A female patient in their mid-50s · history notes alcohol use and prior malignancy (patient or family) · the patient was assessed as Fitzpatrick phototype IV · a clinical photo of a skin lesion taken with a smartphone: 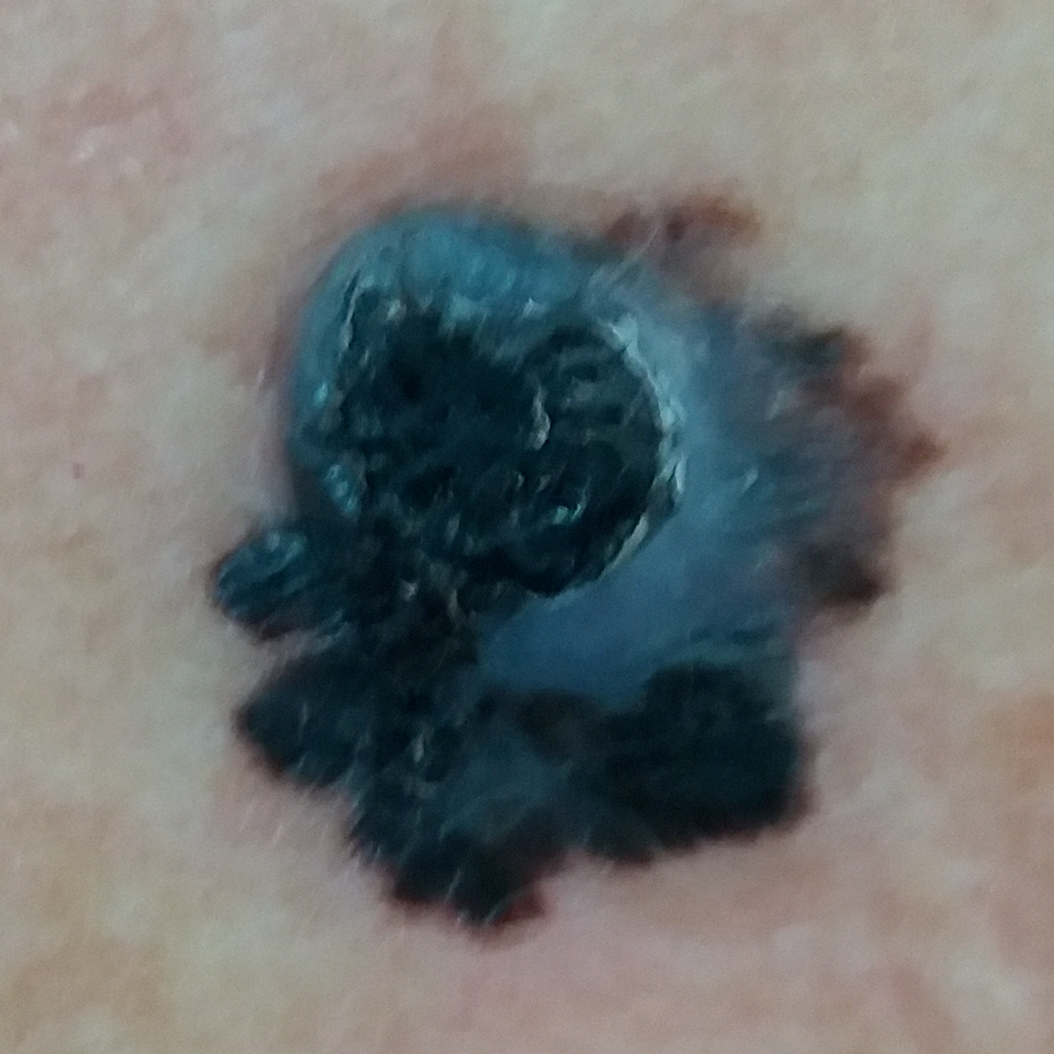anatomic site = the back | size = approx. 14 × 12 mm | diagnostic label = melanoma (biopsy-proven).